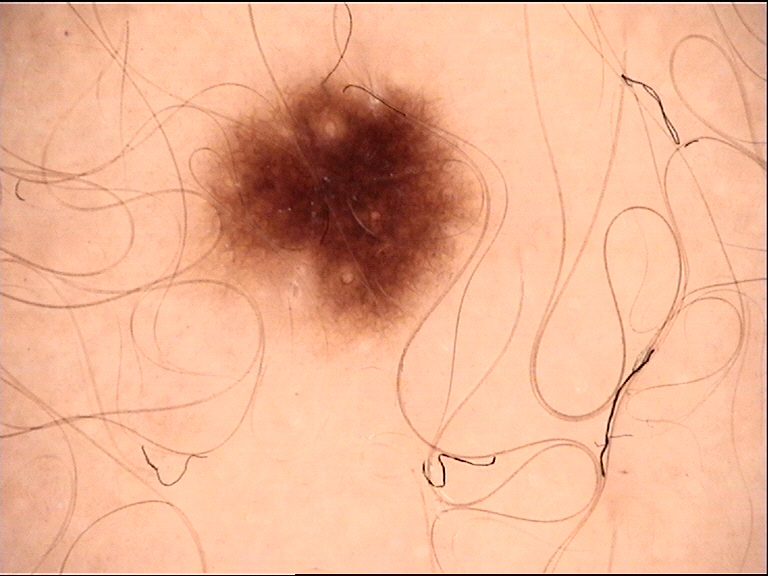The morphology is that of a banal lesion. Classified as a junctional nevus.